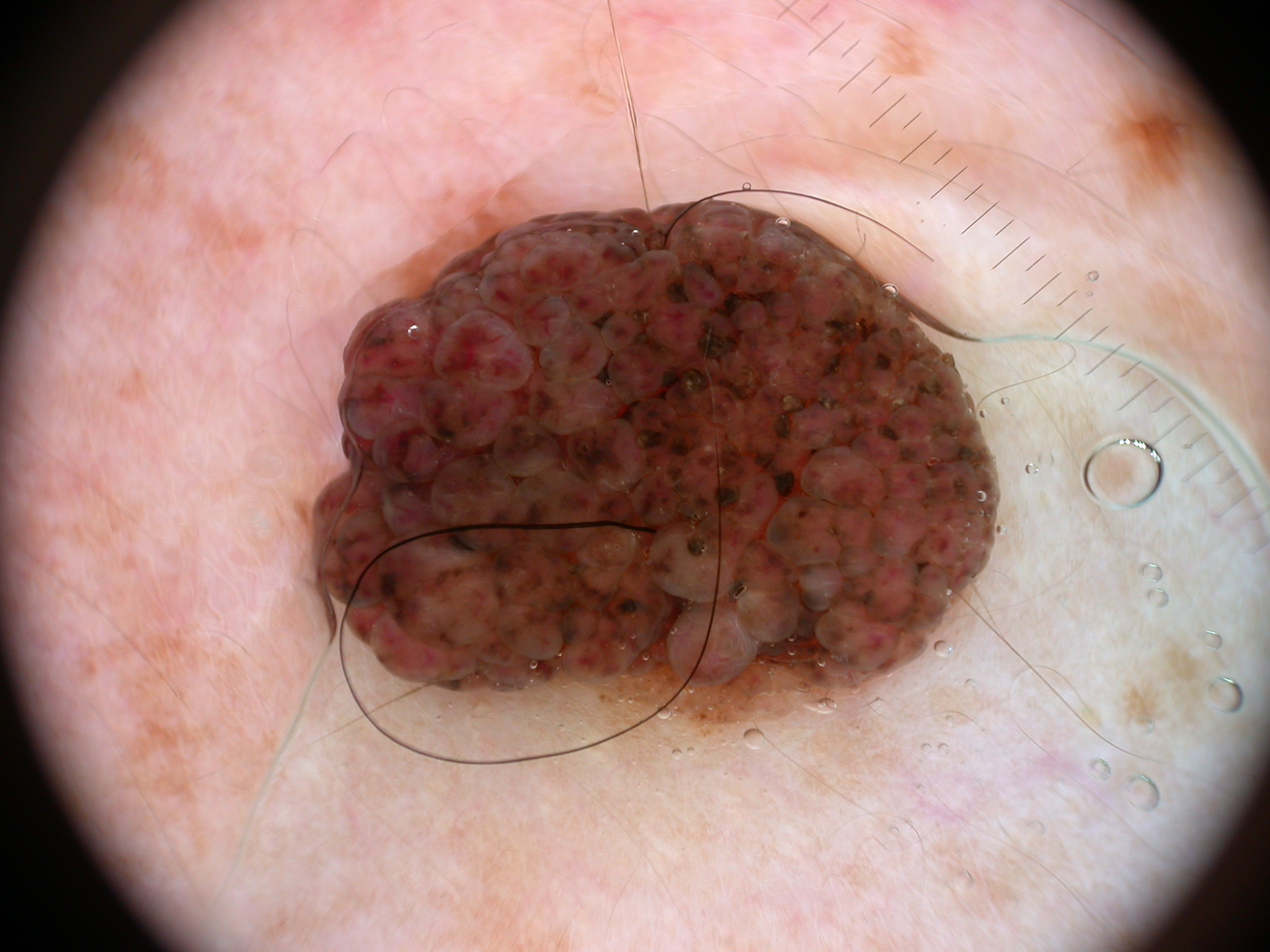{
  "image": {
    "modality": "dermoscopy"
  },
  "dermoscopic_features": {
    "present": [],
    "absent": [
      "negative network",
      "streaks",
      "milia-like cysts",
      "globules",
      "pigment network"
    ]
  },
  "lesion_location": {
    "bbox_xyxy": [
      312,
      199,
      1001,
      731
    ]
  },
  "diagnosis": {
    "name": "melanocytic nevus",
    "malignancy": "benign",
    "lineage": "melanocytic",
    "provenance": "clinical"
  }
}